The patient describes having few moles overall · the patient says their skin reddens with sun exposure · a clinical photograph of a skin lesion · a male subject aged 66.
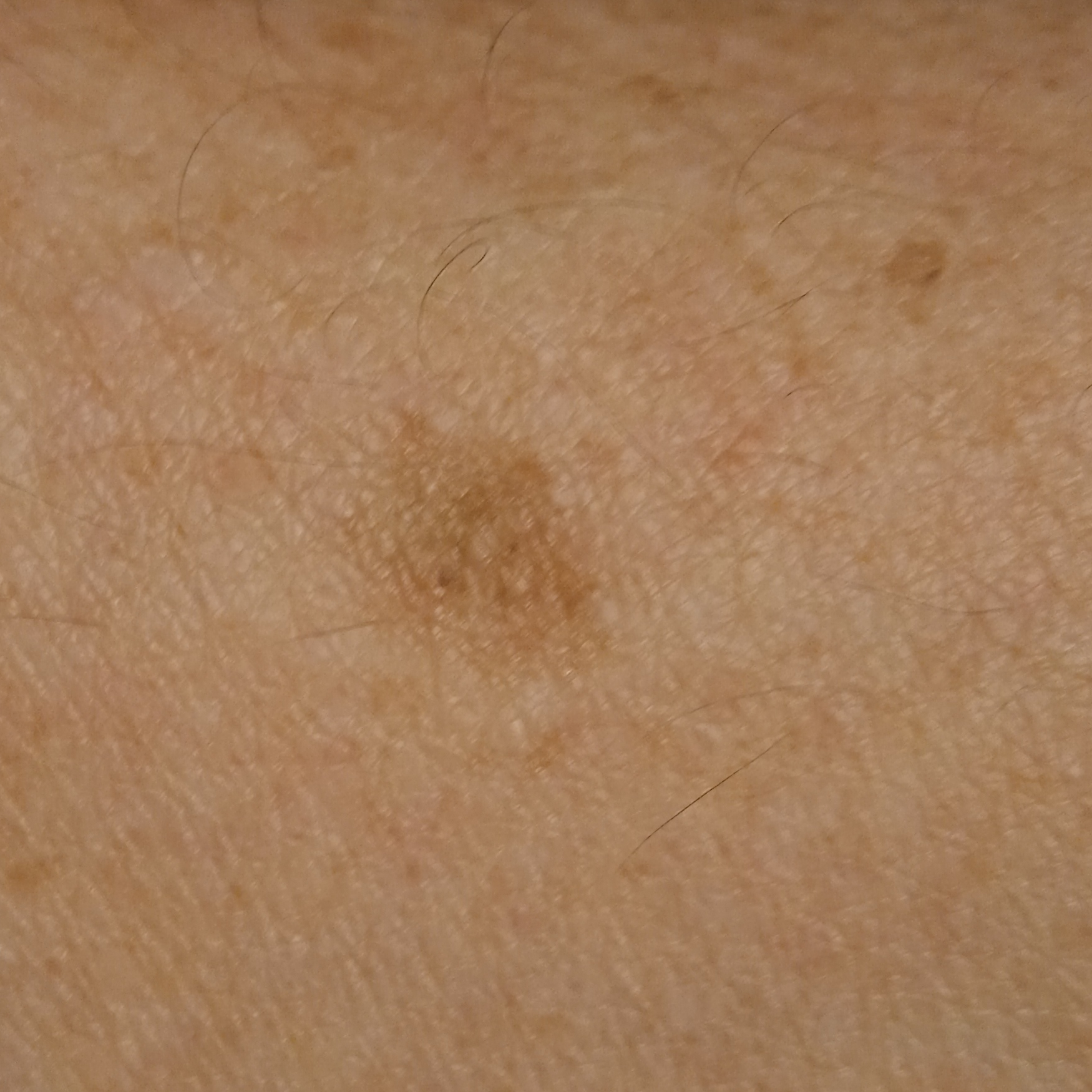Clinical context: Located on an arm. Conclusion: The lesion was assessed as a melanoma.